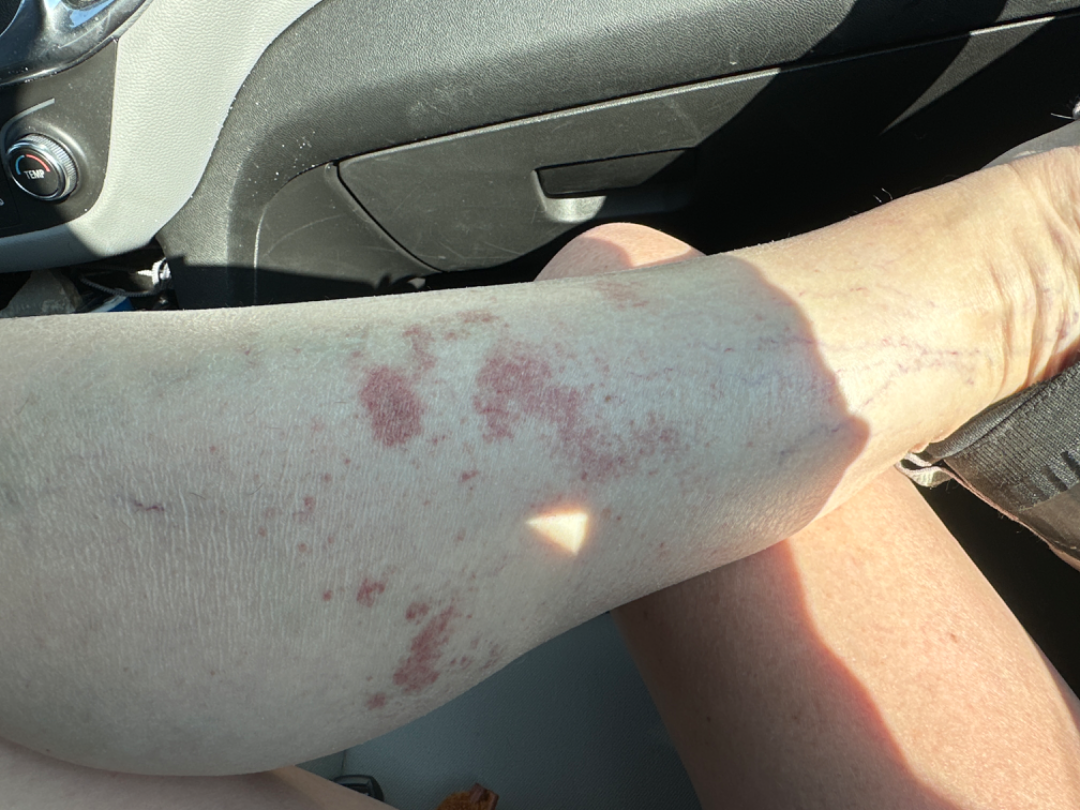{
  "differential": {
    "leading": [
      "Pigmented purpuric eruption"
    ],
    "considered": [
      "Leukocytoclastic Vasculitis"
    ],
    "unlikely": [
      "Allergic Contact Dermatitis"
    ]
  }
}